This image was taken at an angle; located on the head or neck.
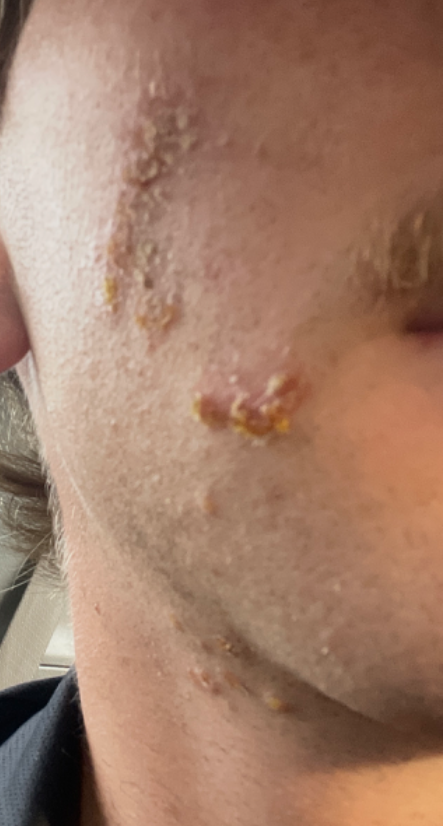Q: What conditions are considered?
A: Impetigo (most likely); Herpes Simplex (considered); Irritant Contact Dermatitis (considered)